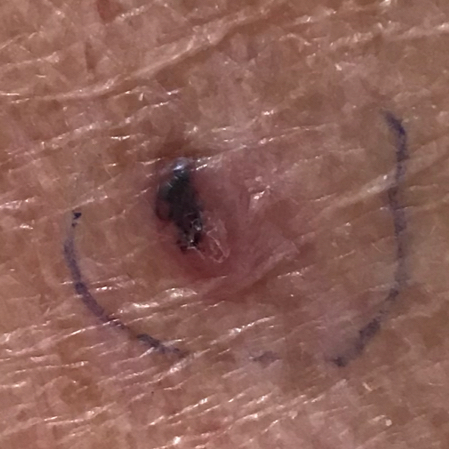A clinical close-up photograph of a skin lesion. The patient was assessed as skin type III. By history, pesticide exposure, prior skin cancer (patient or family), and no alcohol use. A female subject in their 50s. The lesion involves the chest. Measuring about 10 × 5 mm. The patient describes that the lesion has changed, has grown, has bled, and is elevated. The biopsy diagnosis was a malignant skin lesion — a basal cell carcinoma.